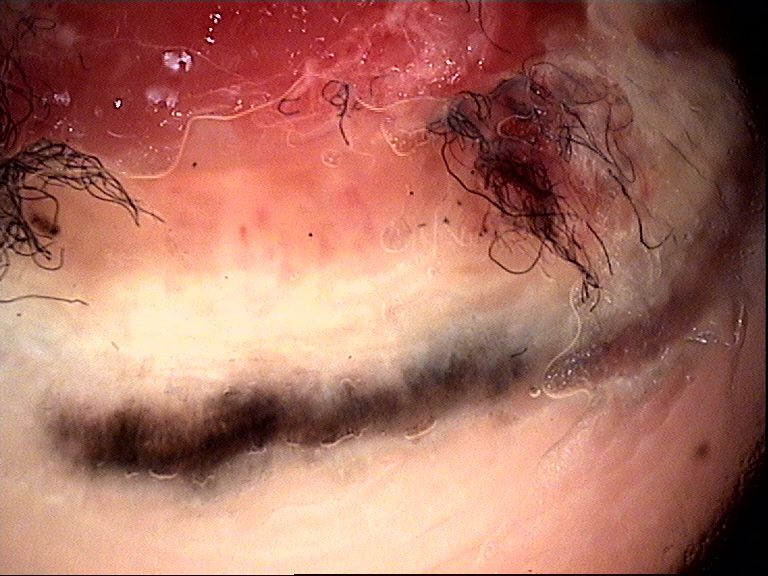The biopsy diagnosis was a malignant lesion — an acral nodular melanoma.